Associated systemic symptoms include mouth sores · this image was taken at a distance · texture is reported as rough or flaky and raised or bumpy · located on the arm, head or neck and sole of the foot · self-categorized by the patient as a rash · the lesion is associated with pain, burning and itching: 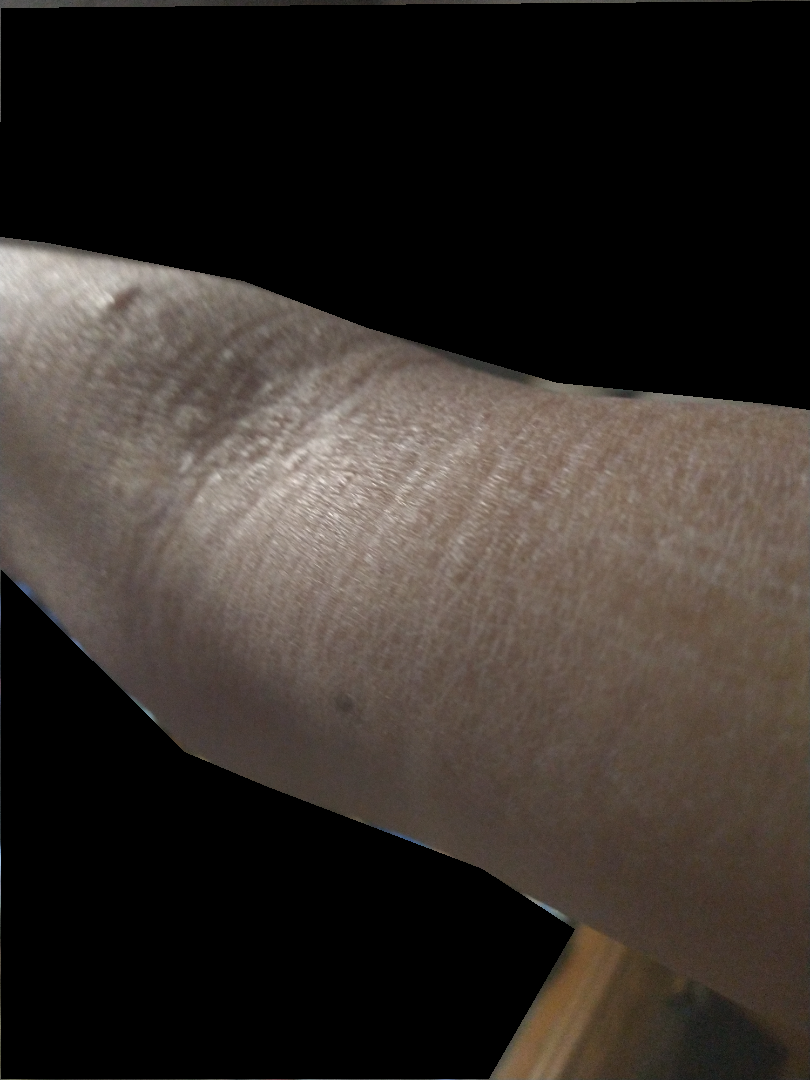{"assessment": "indeterminate"}